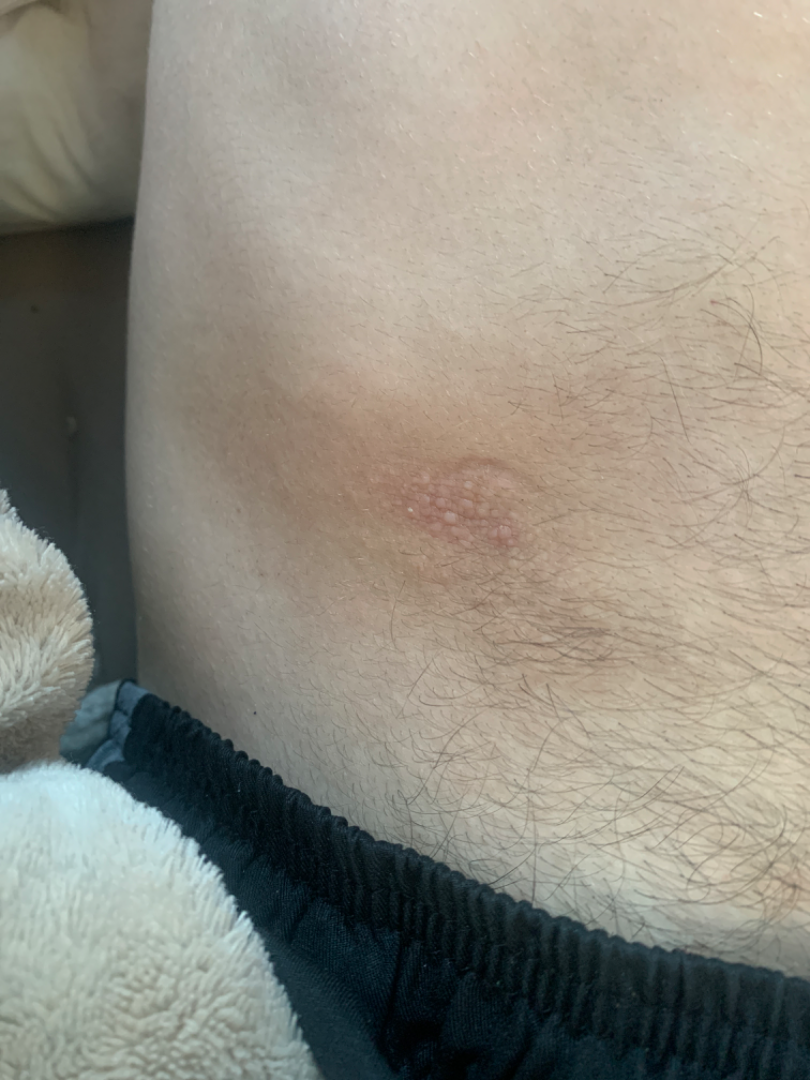assessment: indeterminate
patient: male, age 18–29
shot_type: at a distance